Dermoscopy of a skin lesion.
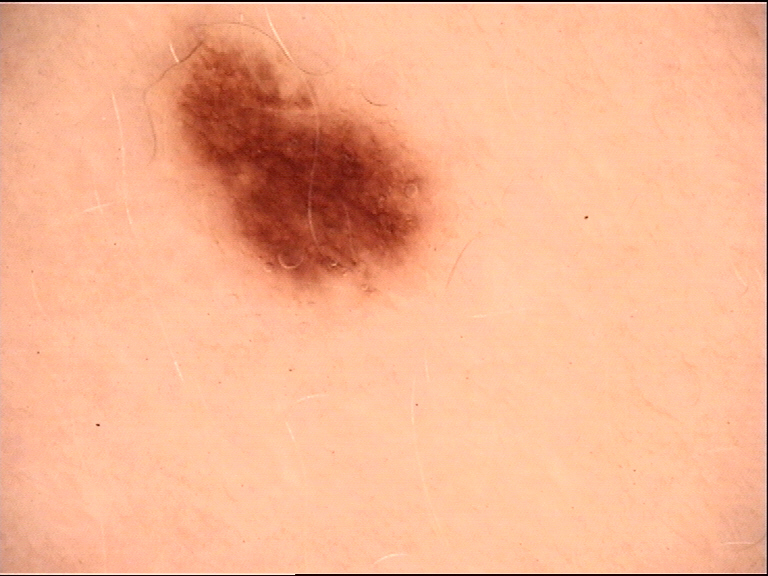The diagnosis was a benign lesion — a dysplastic junctional nevus.